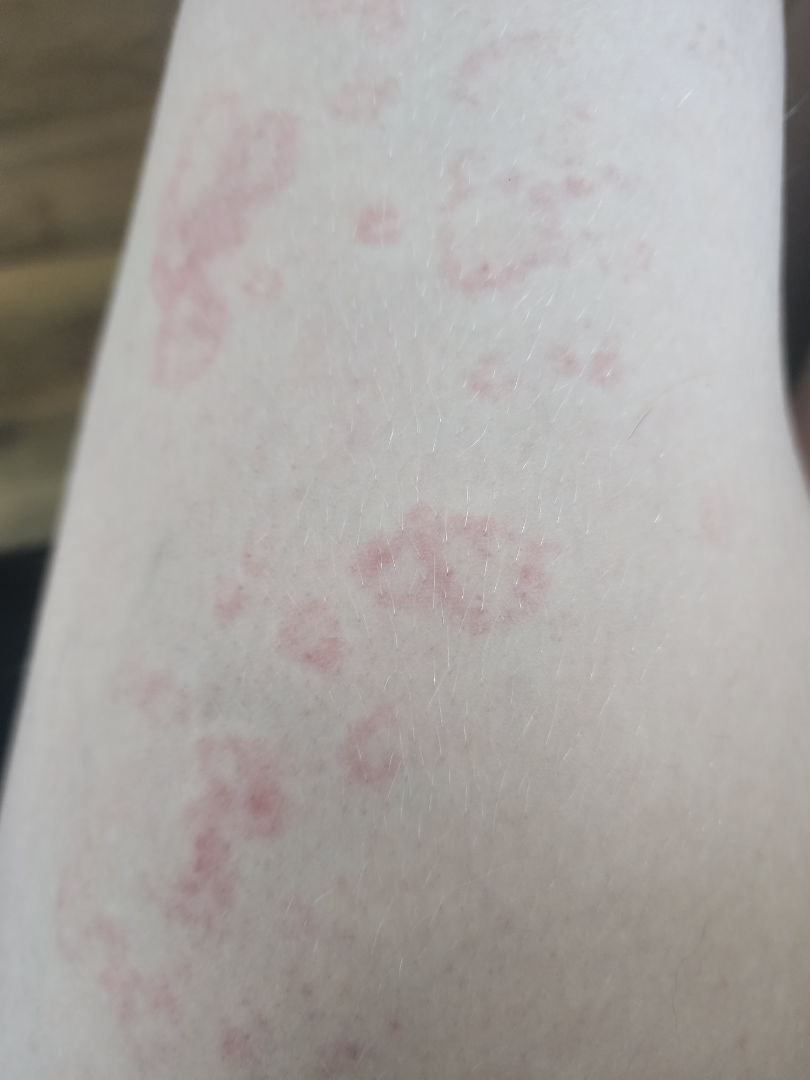patient = female, age 18–29 | site = leg | view = at an angle | dermatologist impression = favoring Urticaria.